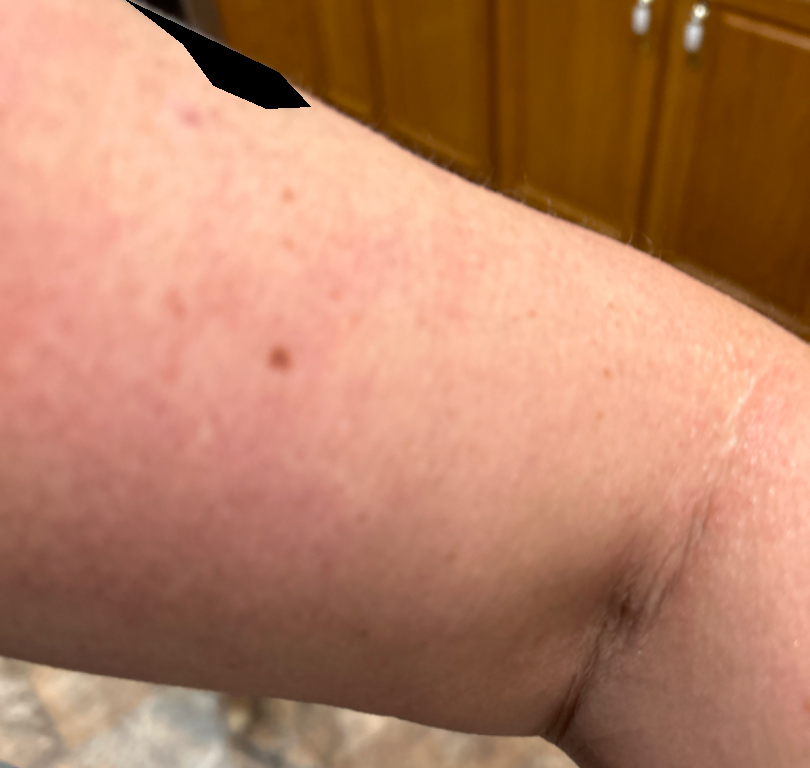Q: Texture?
A: raised or bumpy
Q: What is the framing?
A: at an angle
Q: Age and sex?
A: female, age 40–49
Q: What is the dermatologist's impression?
A: consistent with Eczema